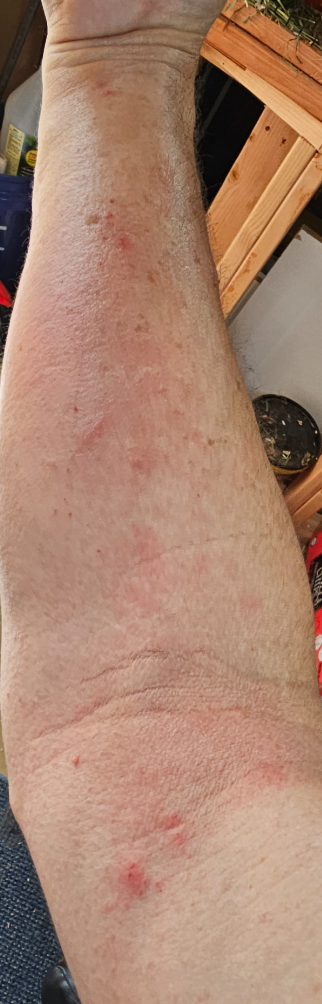Case summary:
– diagnostic considerations · Photodermatitis (weight 0.33); Eczema (weight 0.33); Allergic Contact Dermatitis (weight 0.33)